Self-categorized by the patient as a rash; Fitzpatrick skin type II; the head or neck is involved; the lesion is associated with enlargement and itching; the photo was captured at an angle; the patient indicates the lesion is raised or bumpy: 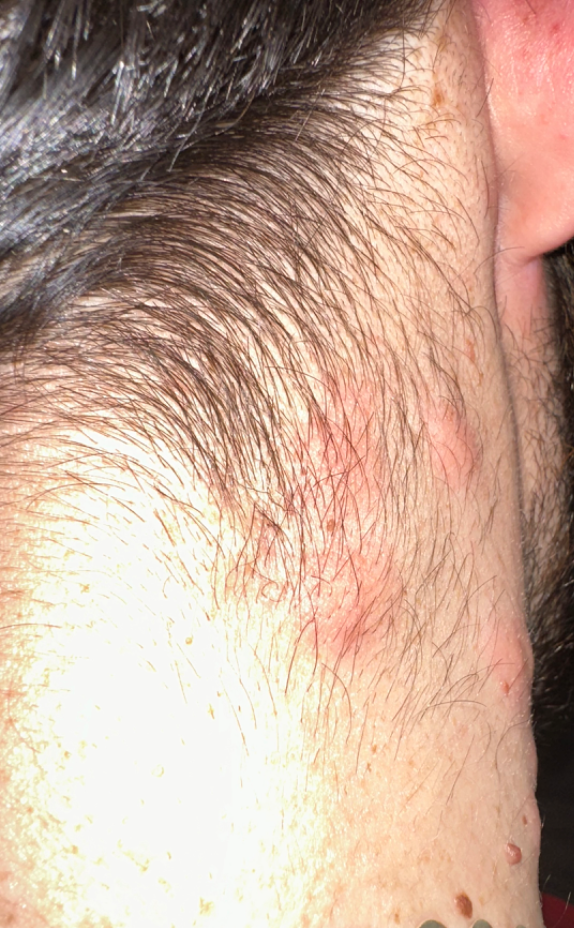On independent review by the dermatologists, the leading impression is Urticaria; less likely is Allergic Contact Dermatitis; less probable is Abscess; a more distant consideration is Granuloma faciale; a remote consideration is Primary cutaneous lymphoma.